A dermoscopic image of a skin lesion:
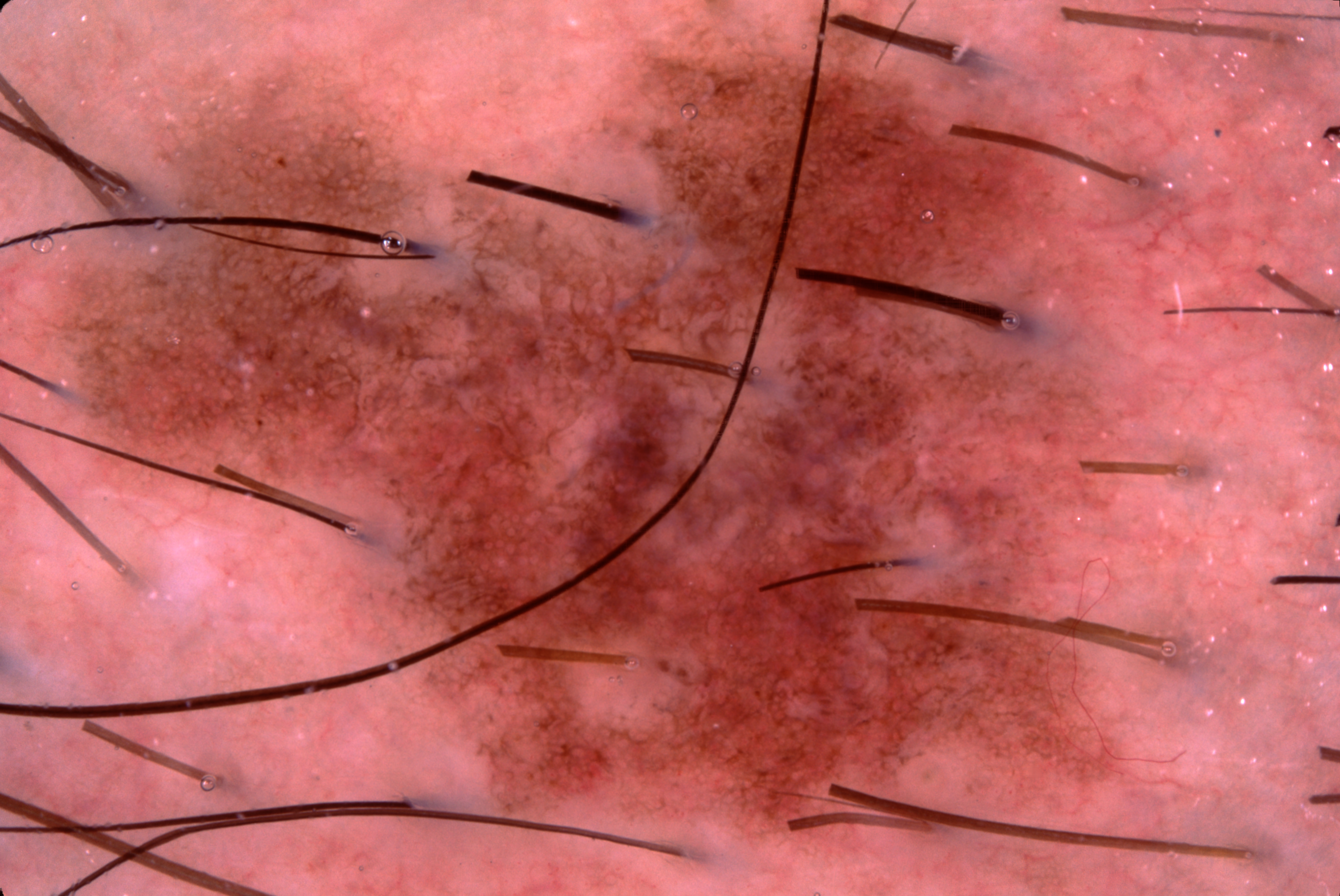dermoscopic features — pigment network; absent: streaks, negative network, and milia-like cysts | size — large | lesion location — bbox=[0, 3, 1175, 870] | diagnostic label — a melanocytic nevus.